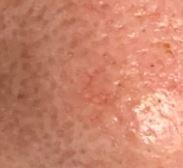Q: Patient demographics?
A: female, aged 63-67
Q: Skin phototype?
A: II
Q: What is the anatomic site?
A: the head or neck
Q: What did the workup show?
A: Basal cell carcinoma (biopsy-proven)